Dermoscopy of a skin lesion.
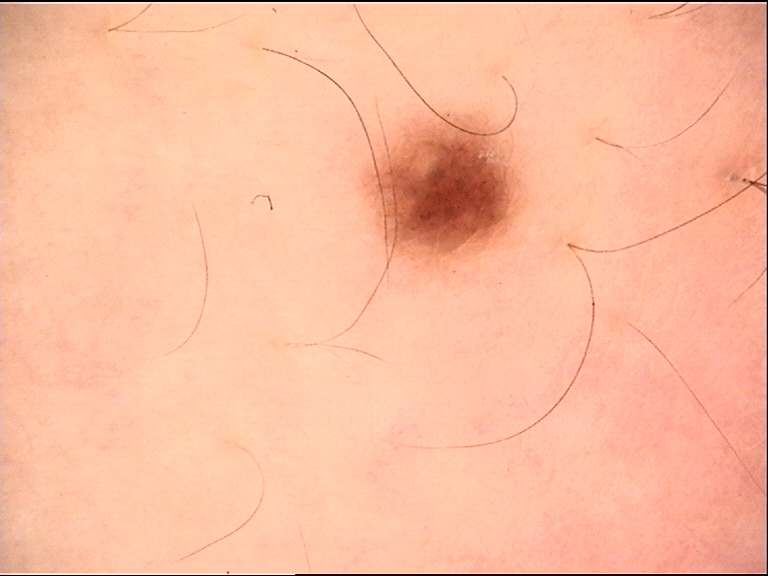- diagnosis · dysplastic junctional nevus (expert consensus)